A dermoscopic photograph of a skin lesion:
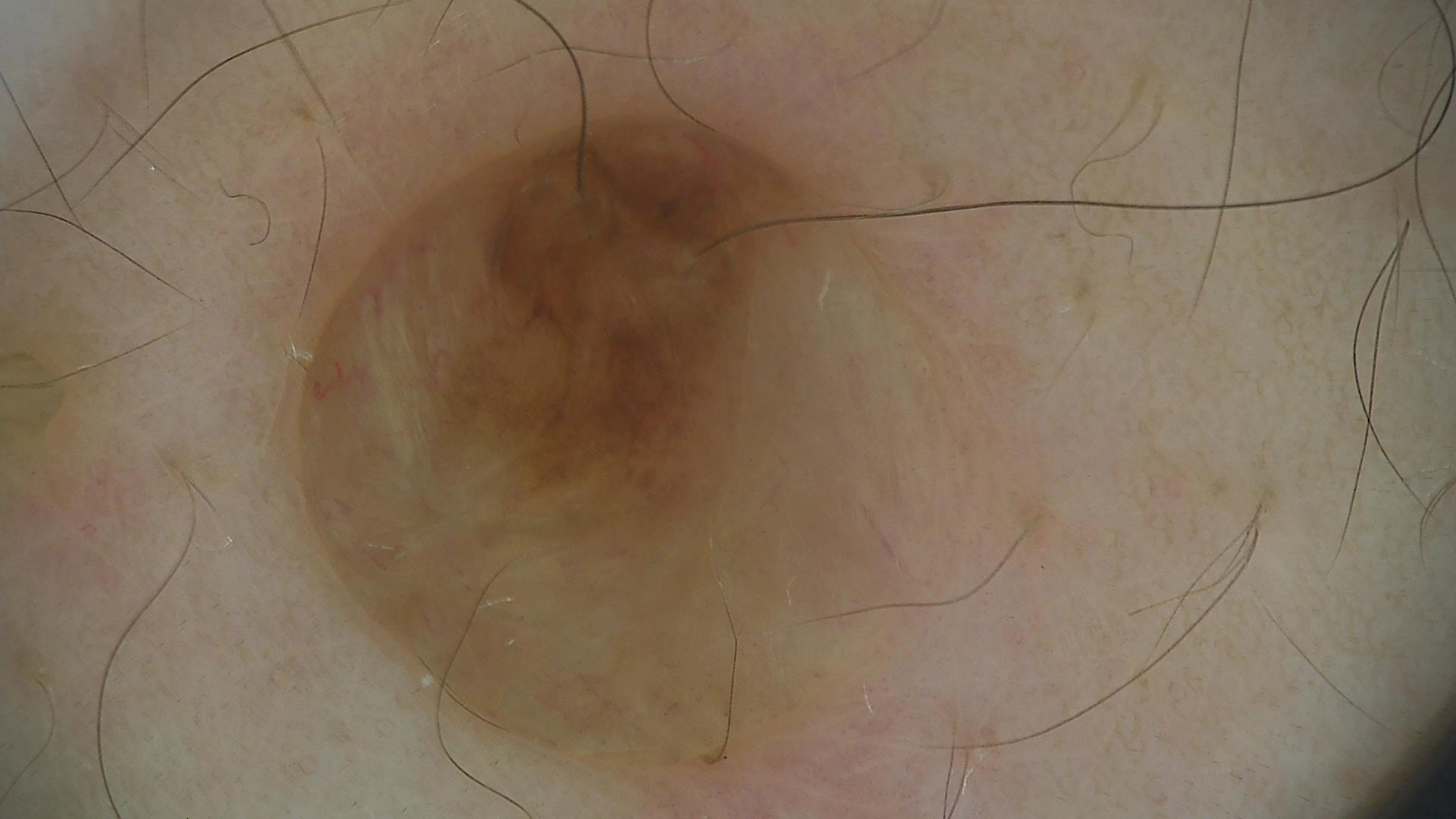lesion type = banal; diagnosis = dermal nevus (expert consensus).